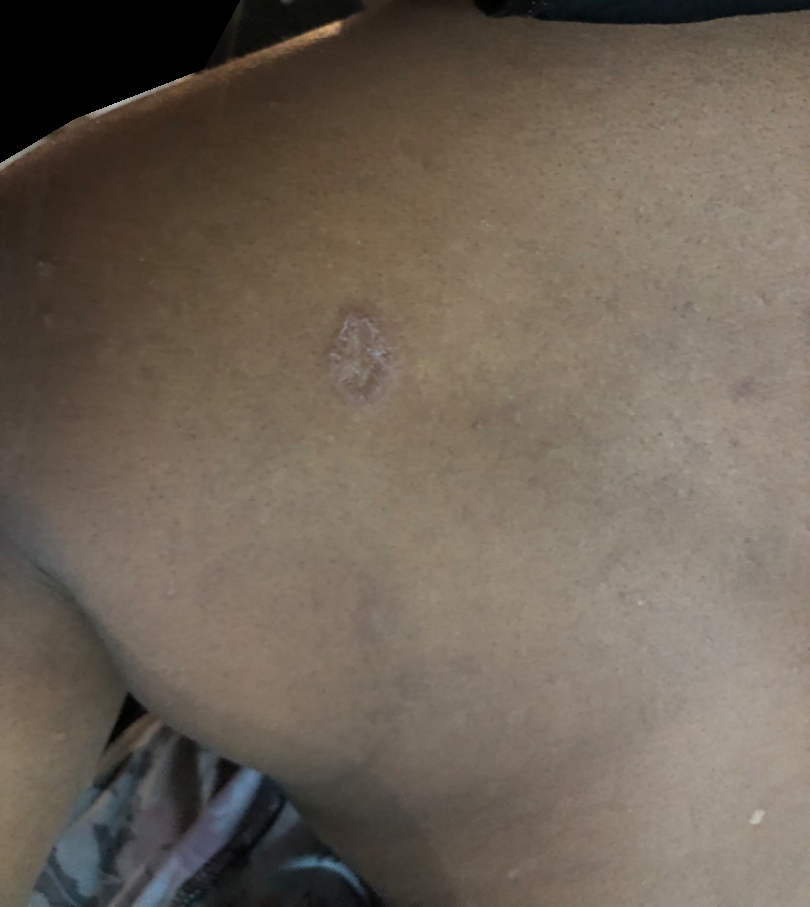history=less than one week | patient=female, age 30–39 | framing=close-up | lesion texture=raised or bumpy | patient describes the issue as=a rash | systemic symptoms=none reported | differential diagnosis=favoring Tinea; also raised was Deep fungal infection; possibly SCC/SCCIS; less likely is Tuberculosis of skin and subcutaneous tissue.